A dermoscopic photograph of a skin lesion.
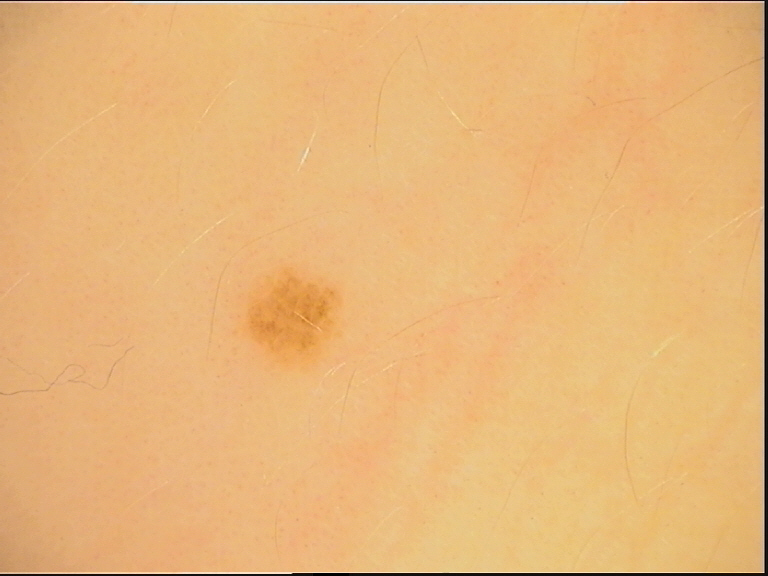<case>
<lesion_type>
<main_class>banal</main_class>
<pattern>junctional</pattern>
</lesion_type>
<diagnosis>
<name>junctional nevus</name>
<code>jb</code>
<malignancy>benign</malignancy>
<super_class>melanocytic</super_class>
<confirmation>expert consensus</confirmation>
</diagnosis>
</case>